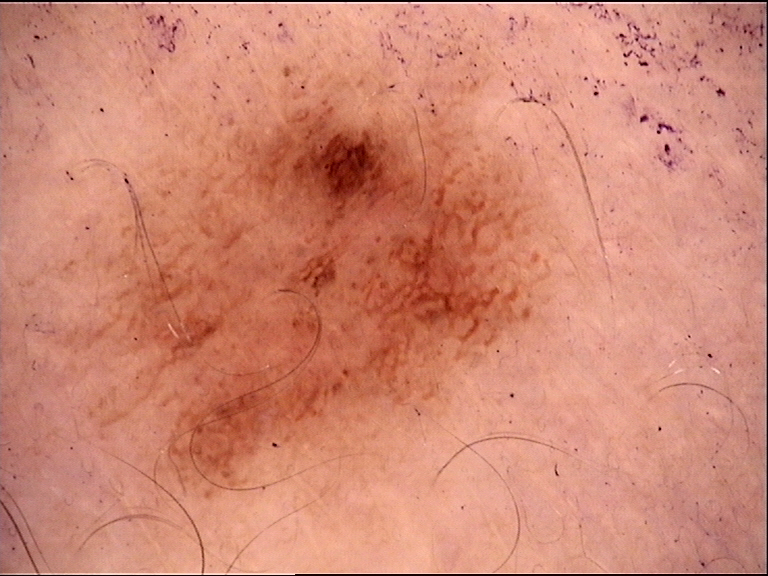  image: dermoscopy
  diagnosis:
    name: dysplastic junctional nevus
    code: jd
    malignancy: benign
    super_class: melanocytic
    confirmation: expert consensus